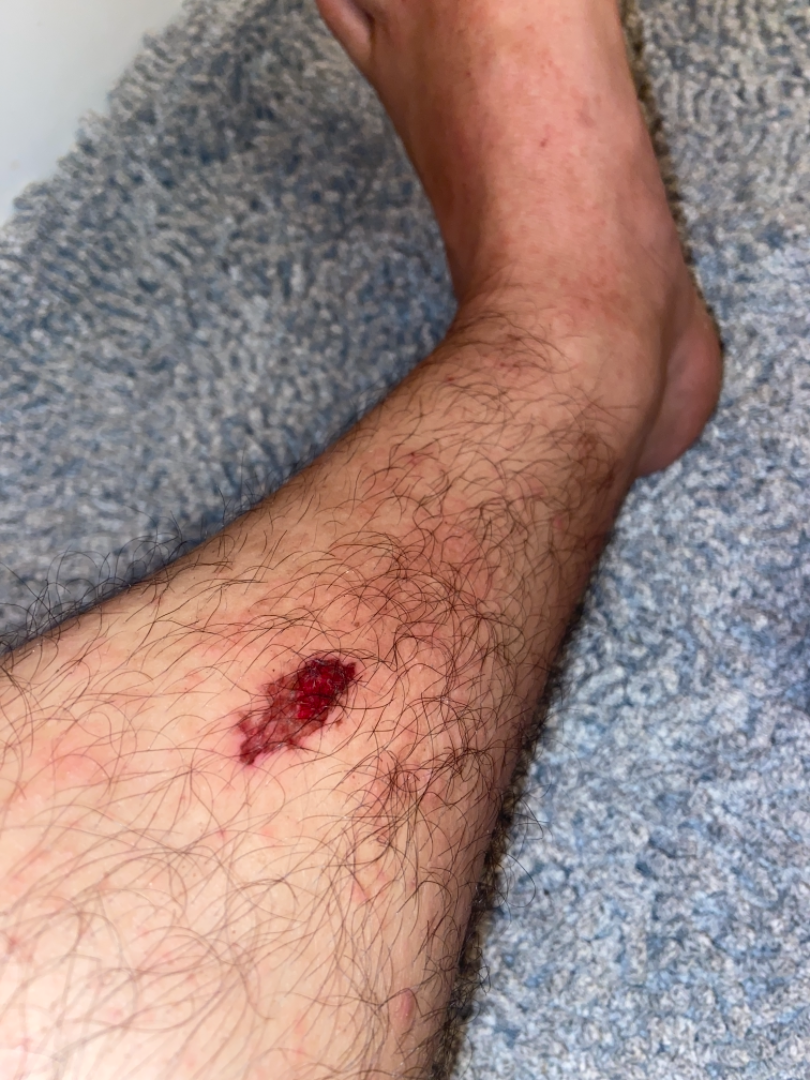Q: What was the assessment?
A: ungradable on photographic review
Q: How long has this been present?
A: one to four weeks
Q: Texture?
A: raised or bumpy
Q: What is the patient's skin tone?
A: Fitzpatrick IV
Q: Age and sex?
A: male, age 18–29
Q: How does the patient describe it?
A: a rash
Q: Where on the body?
A: leg
Q: Constitutional symptoms?
A: none reported
Q: Image view?
A: at an angle
Q: What symptoms does the patient report?
A: bleeding, enlargement and itching